Dermoscopy of a skin lesion: 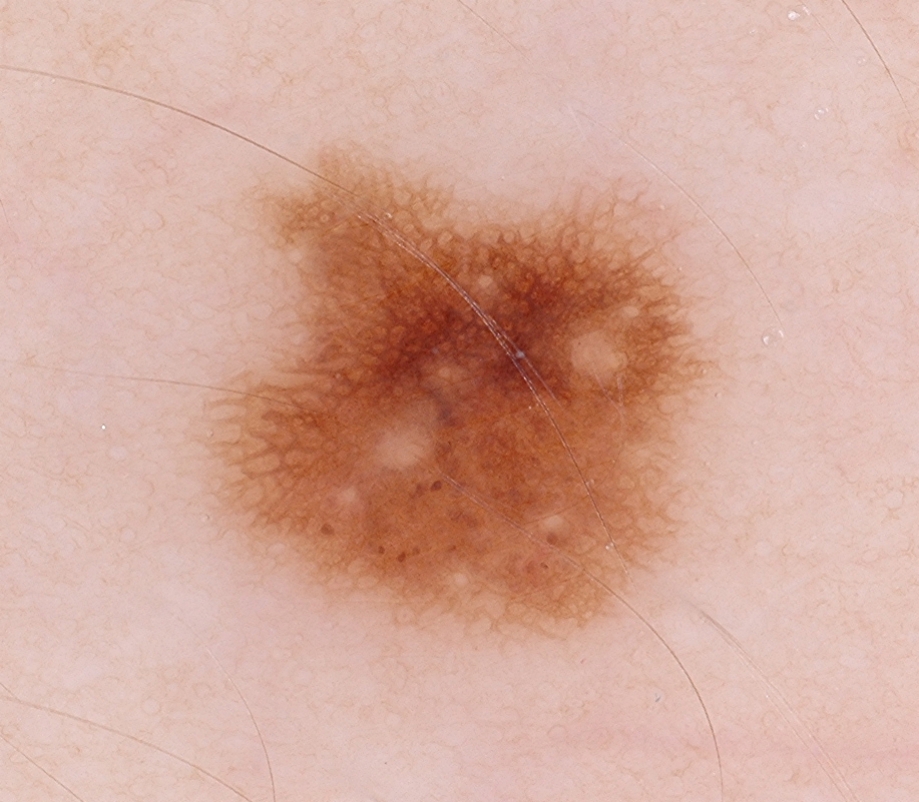With coordinates (x1, y1, x2, y2), lesion location: 203 148 709 637.
Dermoscopically, the lesion shows globules and pigment network, with no negative network, milia-like cysts, or streaks.
Diagnosed as a melanocytic nevus.